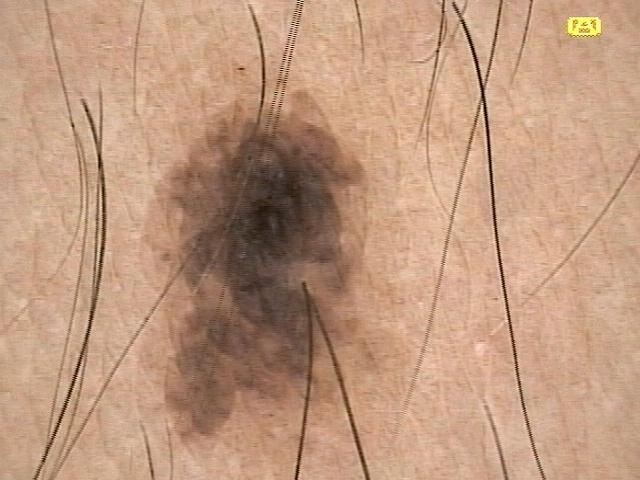imaging: contact-polarized dermoscopy
patient: male, about 35 years old
anatomic site: the head or neck
diagnostic label: Nevus (clinical impression)